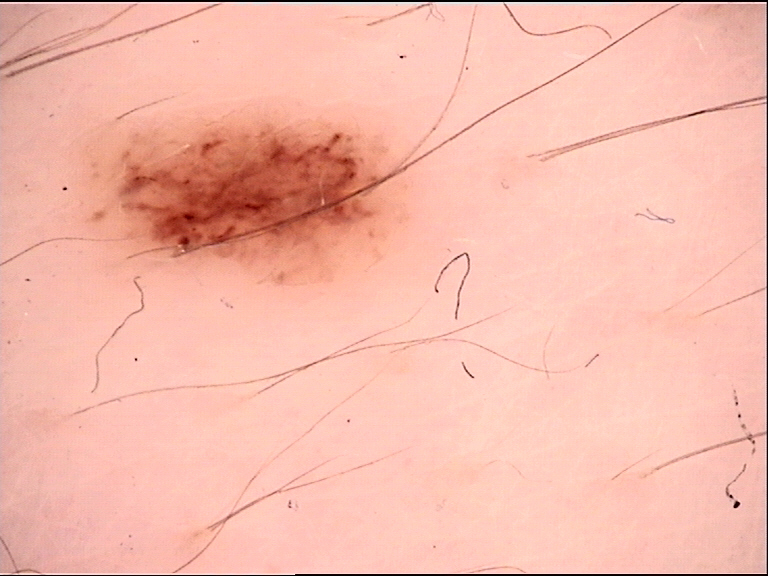Summary:
A dermatoscopic image of a skin lesion.
Impression:
The diagnostic label was a benign lesion — a dysplastic junctional nevus.